A dermoscopy image of a single skin lesion; the subject is a male aged approximately 75.
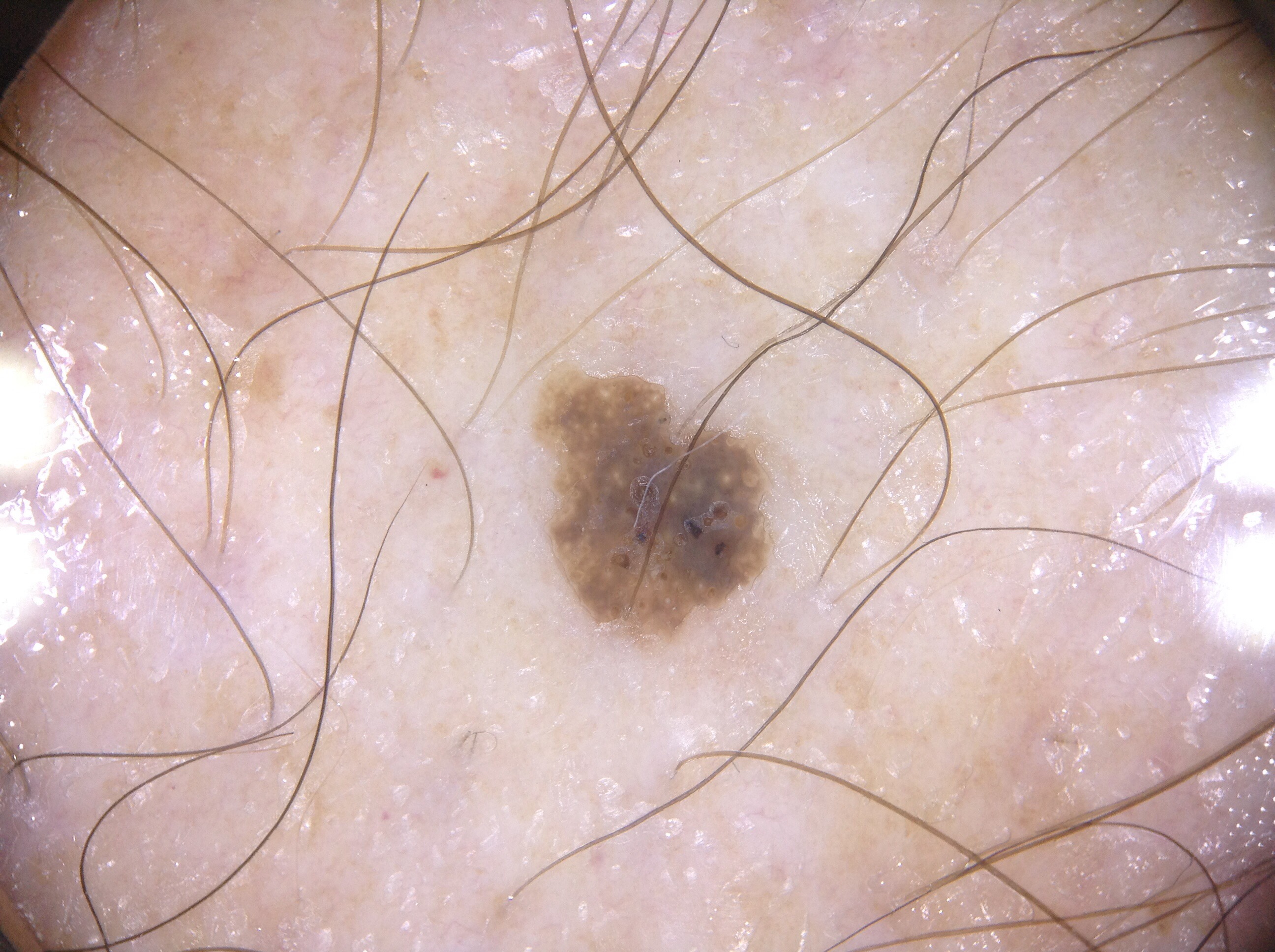Dermoscopic assessment notes milia-like cysts. The lesion occupies the region left=548, top=387, right=767, bottom=632. Expert review diagnosed this as a seborrheic keratosis.